A male subject in their 80s; a clinical close-up photograph of a skin lesion:
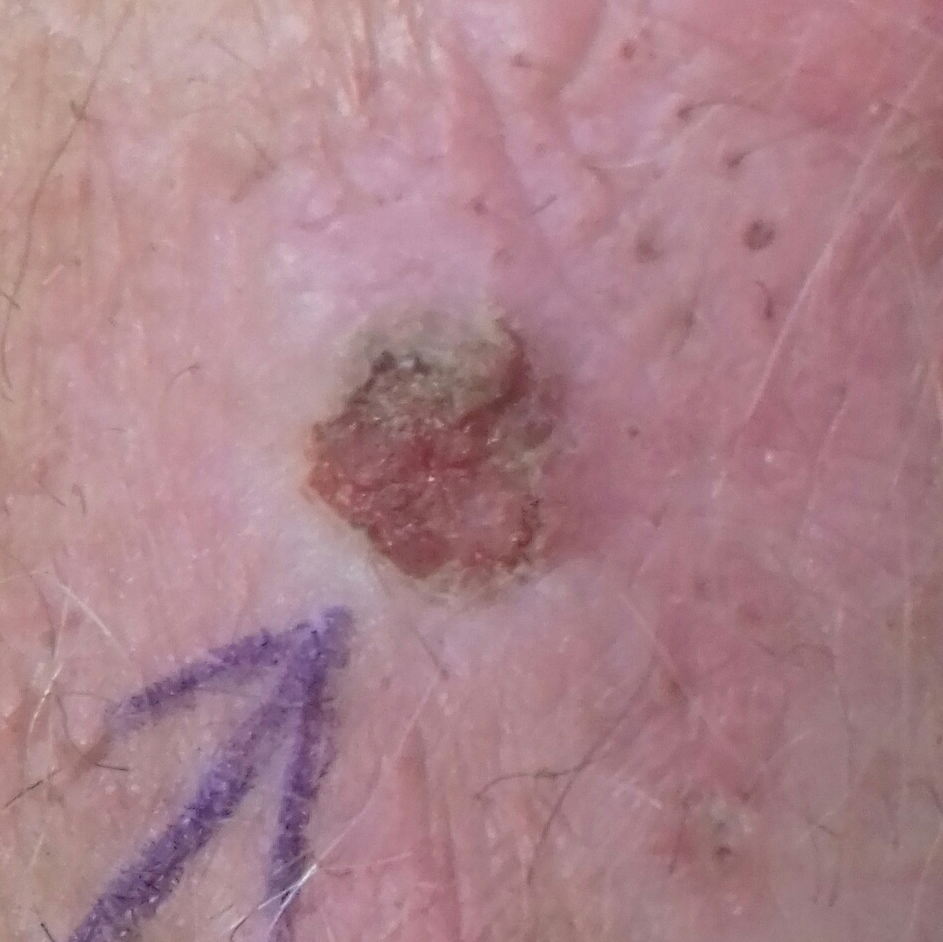By the patient's account, the lesion itches and is elevated, but has not grown. Biopsy-confirmed as an actinic keratosis.